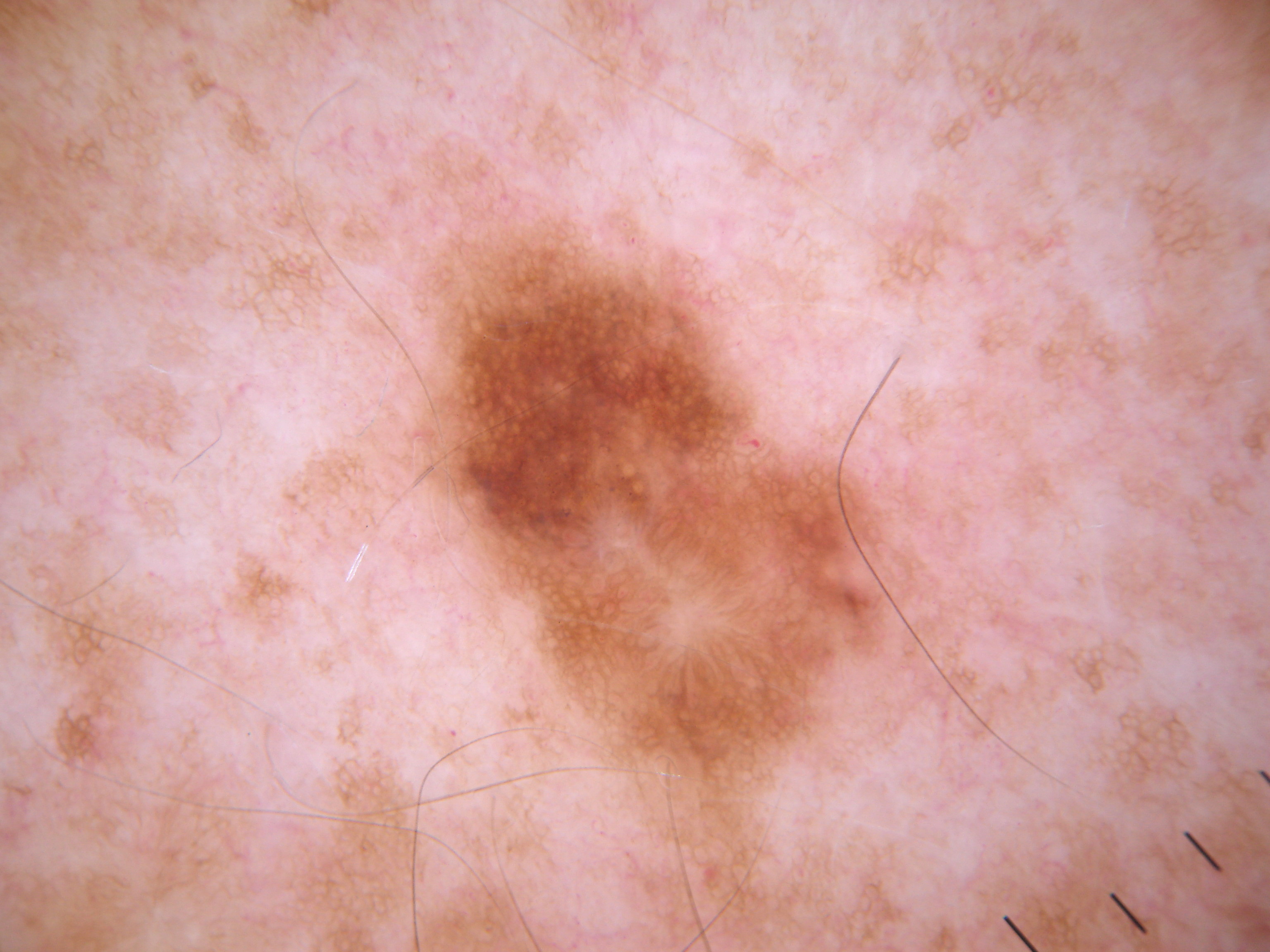Dermoscopy of a skin lesion. In (x1, y1, x2, y2) order, lesion location: [376, 185, 946, 814]. Dermoscopy demonstrates globules and pigment network, with no milia-like cysts, streaks, or negative network. Consistent with a melanocytic nevus.